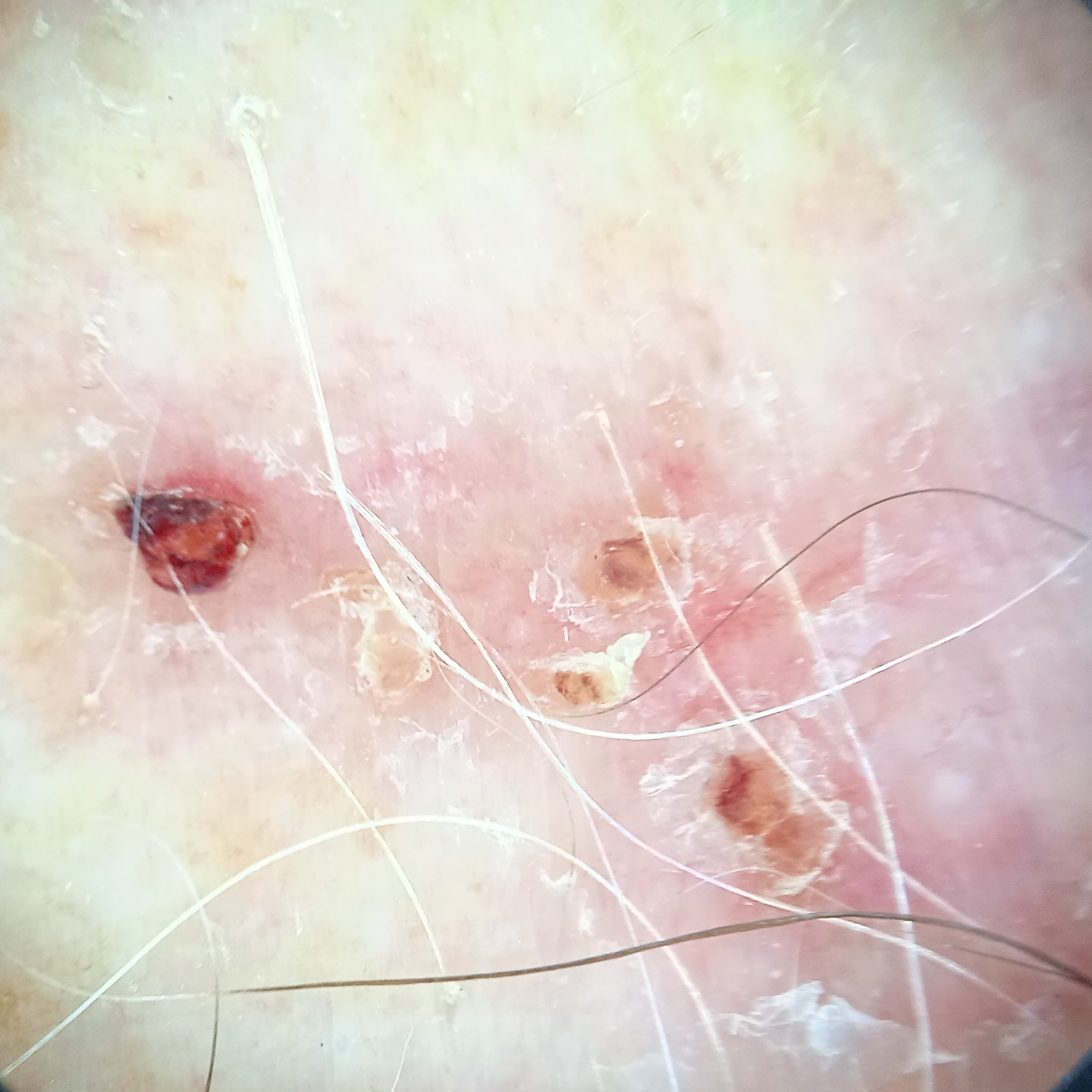A dermatoscopic image of a skin lesion. The lesion is located on the torso. The lesion measures approximately 19 mm. The biopsy diagnosis was a basal cell carcinoma, following a punch biopsy, with tumor thickness 0.8 mm.